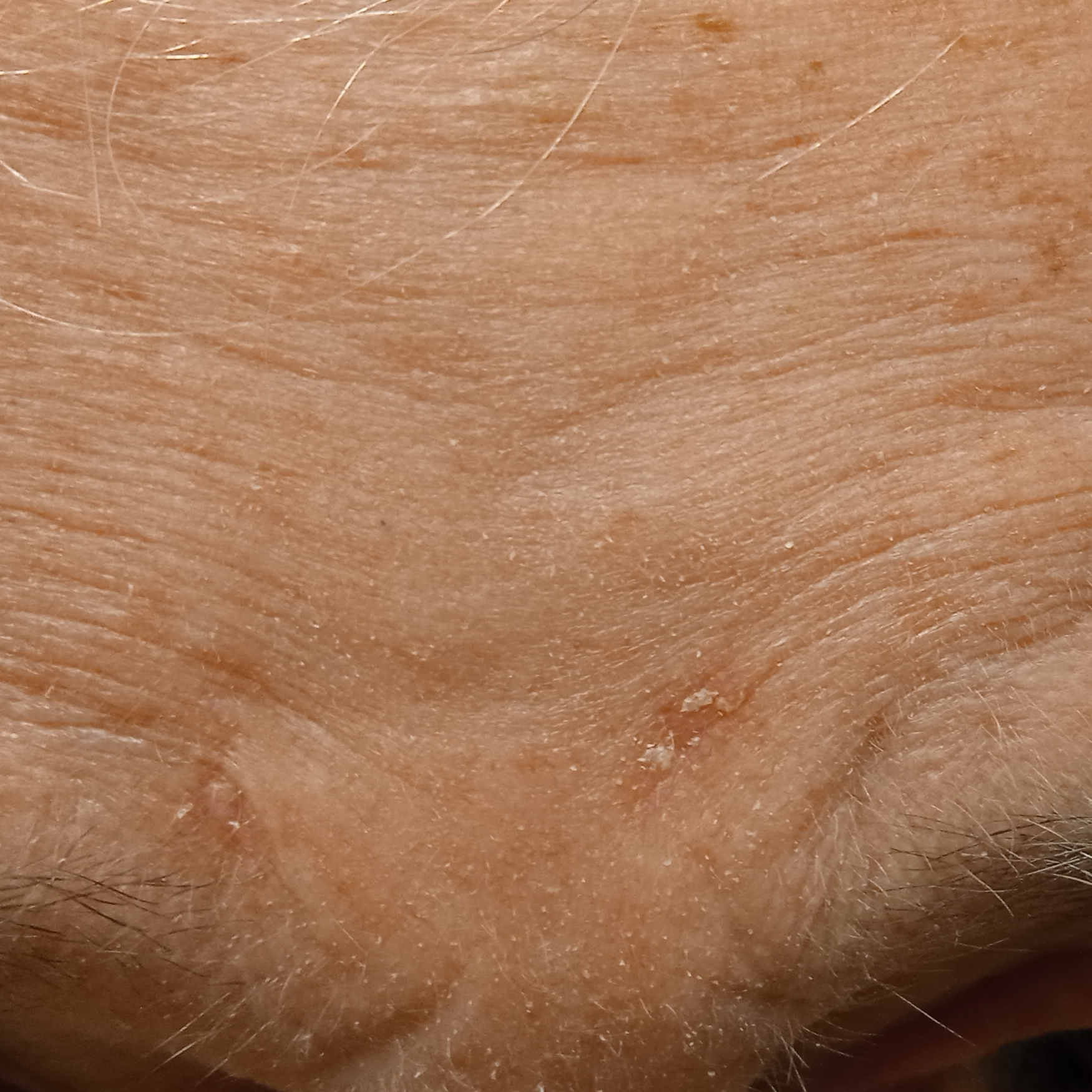patient = male, 83 years old
sun reaction = skin reddens with sun exposure
image type = clinical photograph
lesion size = 7.5 mm
diagnostic label = actinic keratosis (dermatologist consensus)